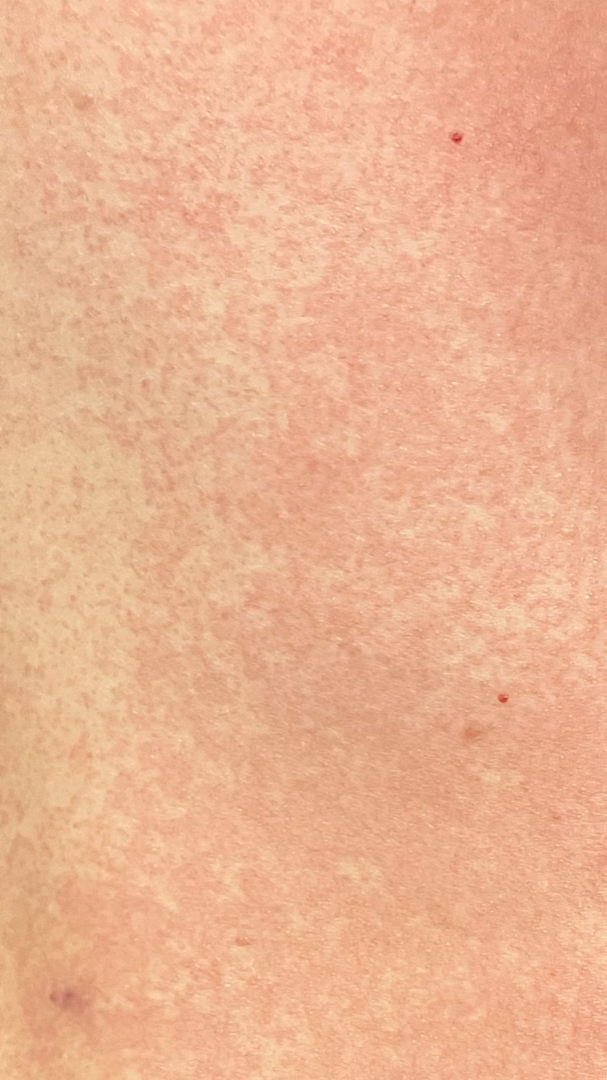Case summary:
- impression: the differential, in no particular order, includes Drug Rash, Viral Exanthem and Urticaria